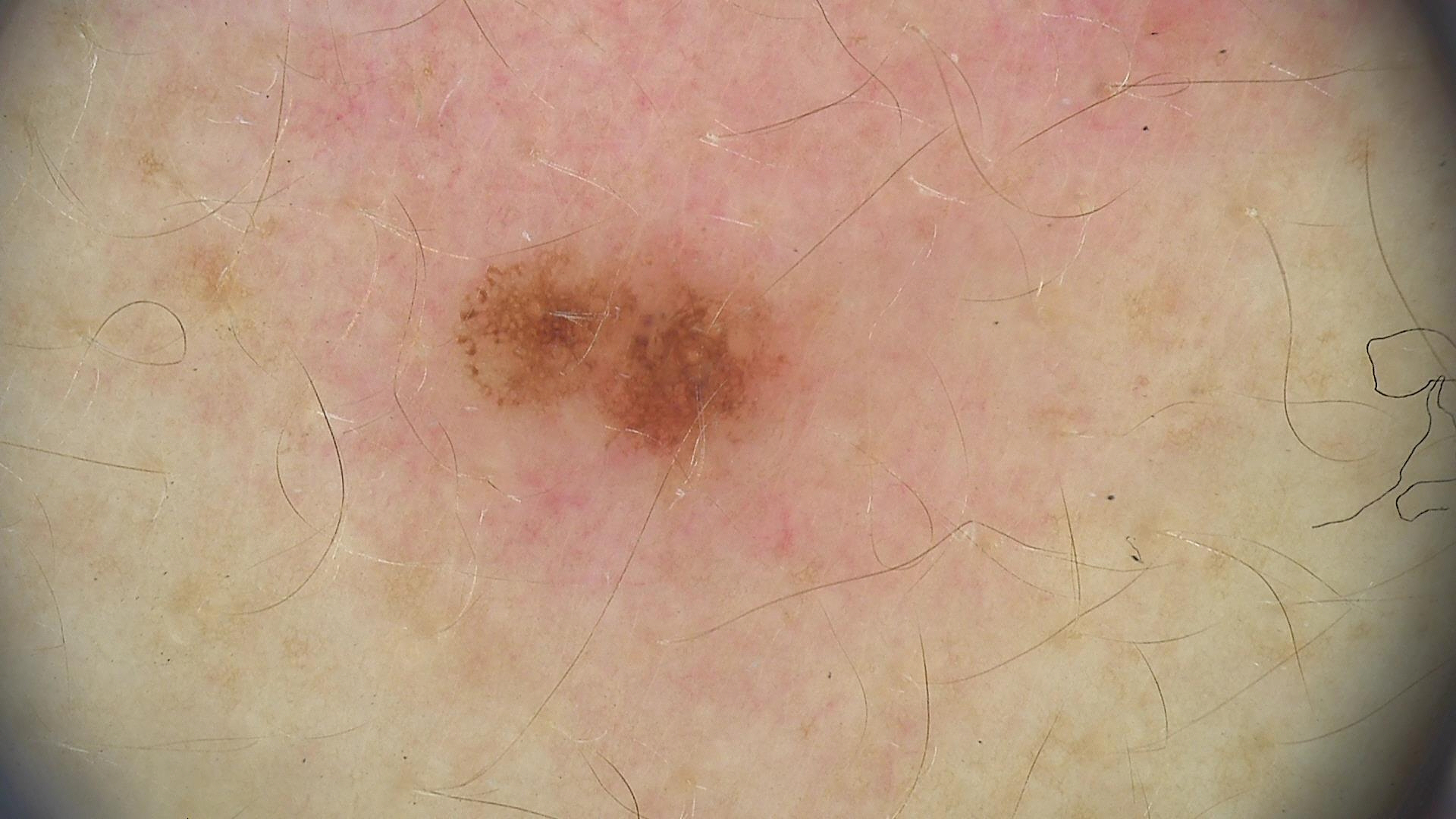The diagnosis was a dysplastic junctional nevus.